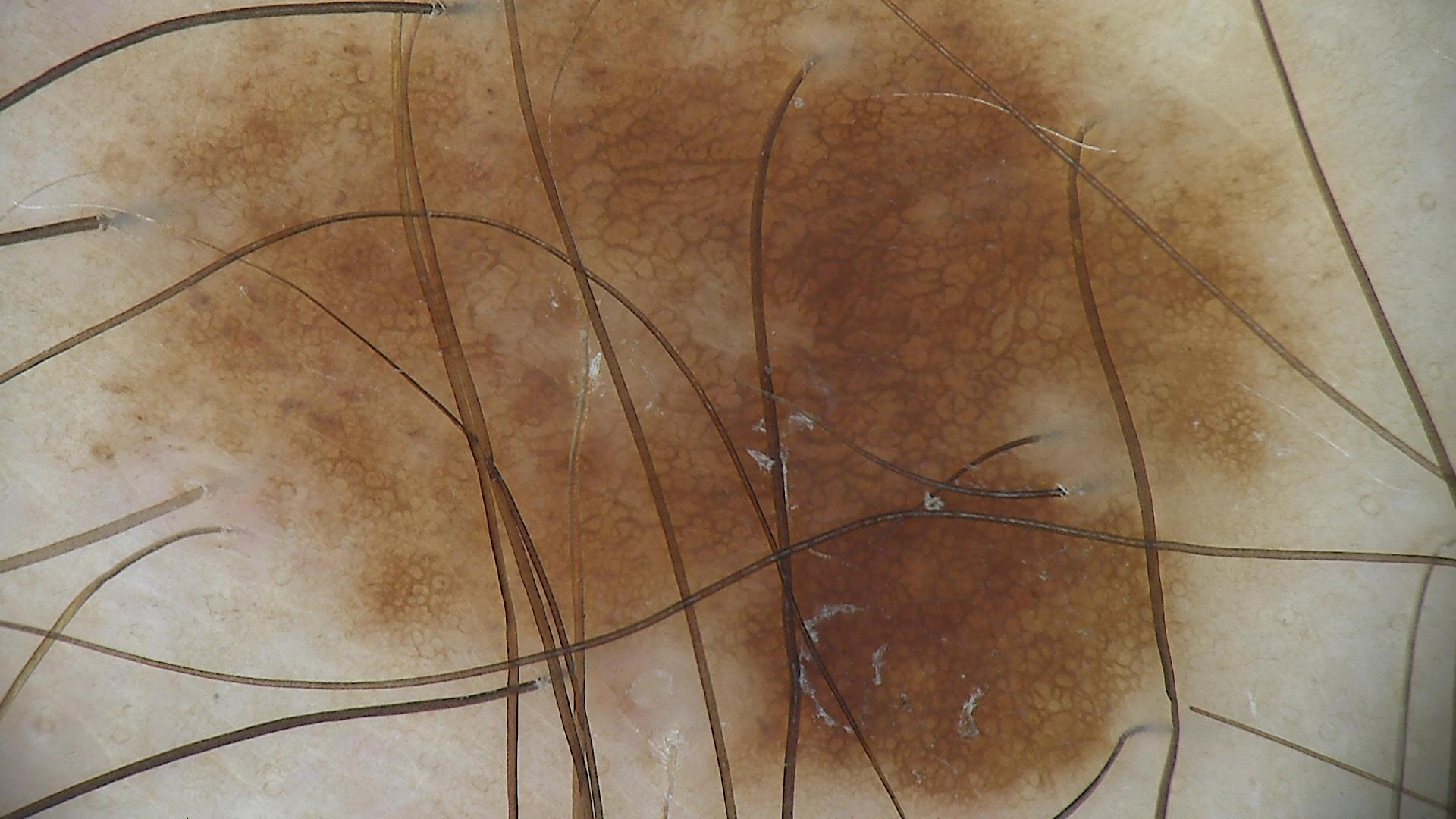Conclusion: Labeled as a dysplastic junctional nevus.